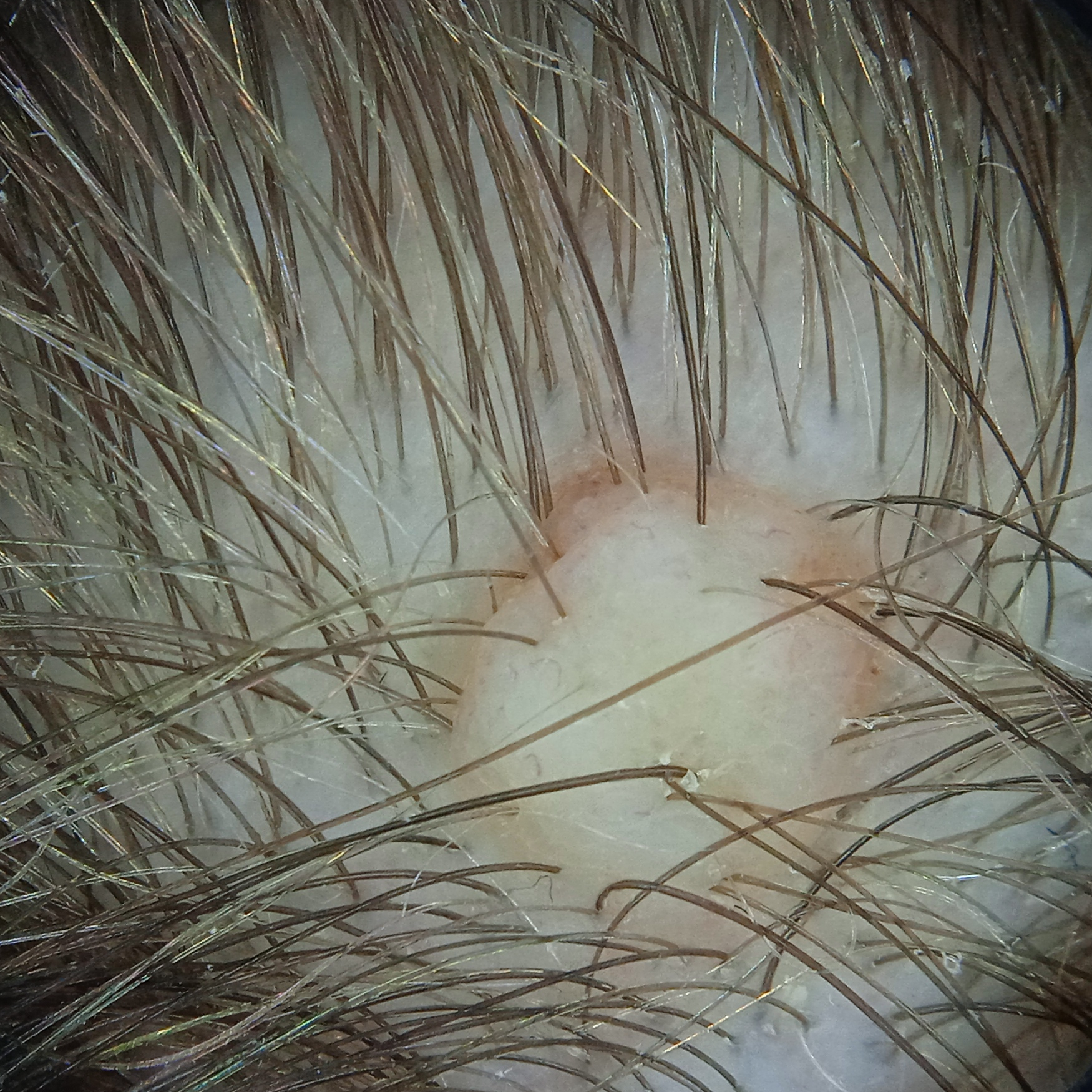Referred for assessment of suspected melanocytic nevus. A dermoscopic image of a skin lesion. A female patient 15 years old. The lesion is on the head. Measuring roughly 5 mm. Histopathologically confirmed as a melanocytic nevus, following excision.